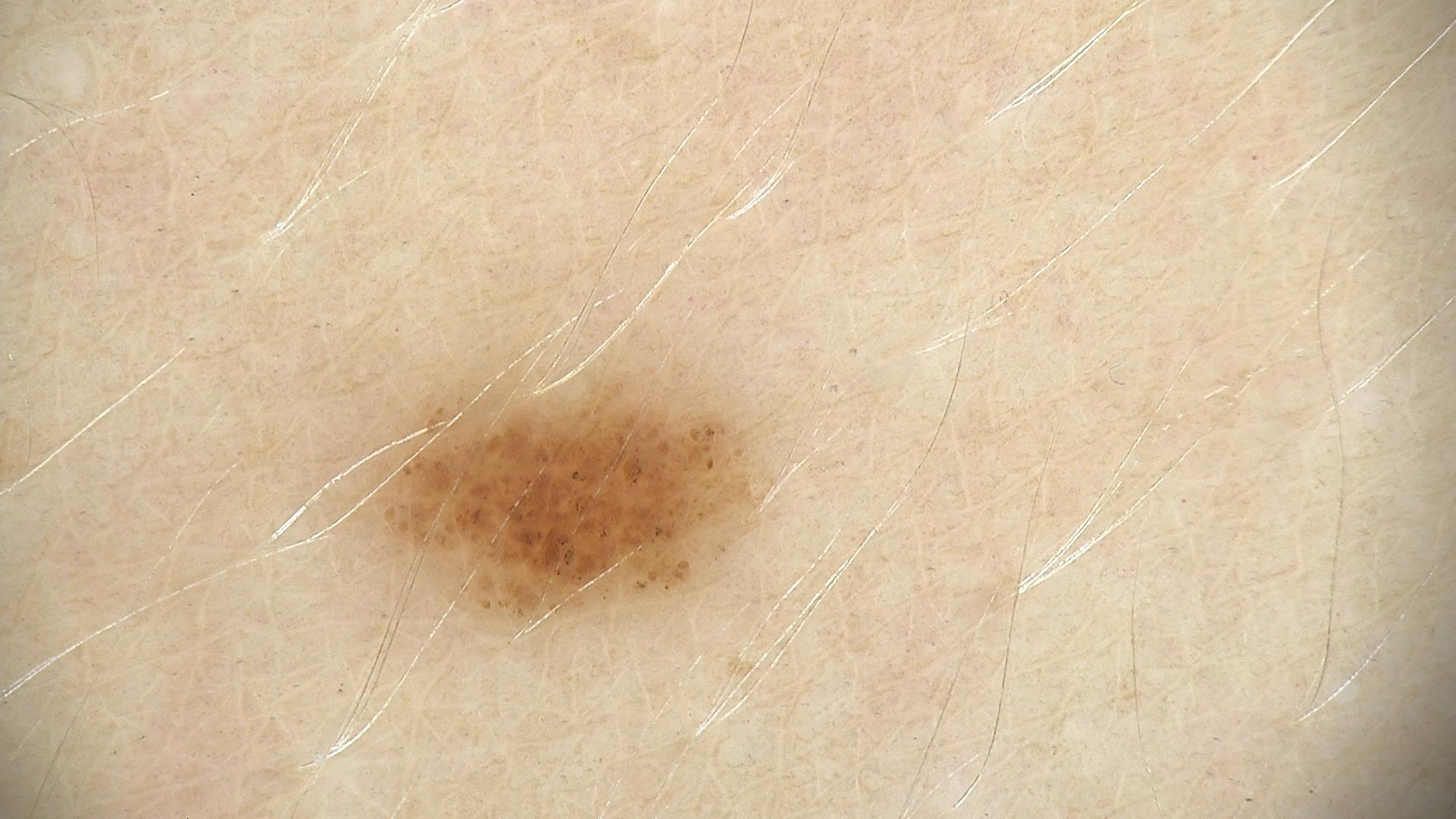Summary: A dermoscopic close-up of a skin lesion. Impression: The diagnosis was a dysplastic junctional nevus.